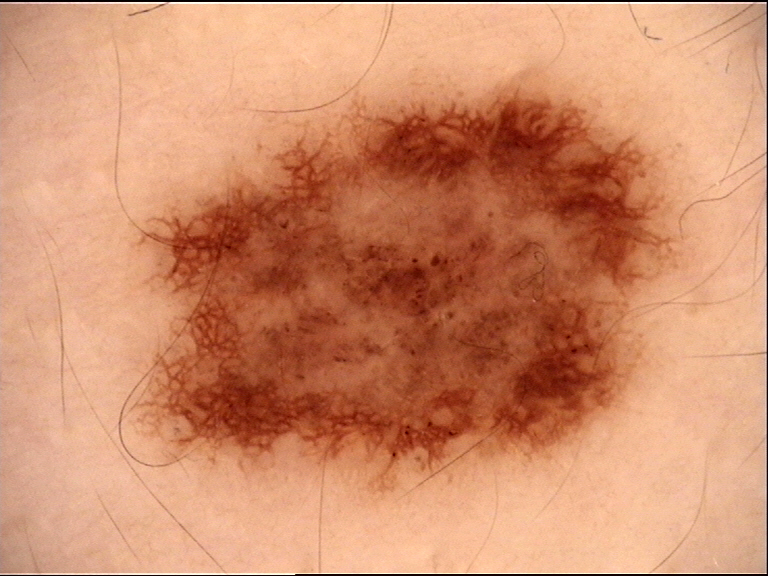Labeled as a dysplastic junctional nevus.